The lesion is described as rough or flaky, raised or bumpy and fluid-filled. The affected area is the back of the hand, leg and arm. The photograph was taken at an angle. Self-categorized by the patient as a rash.
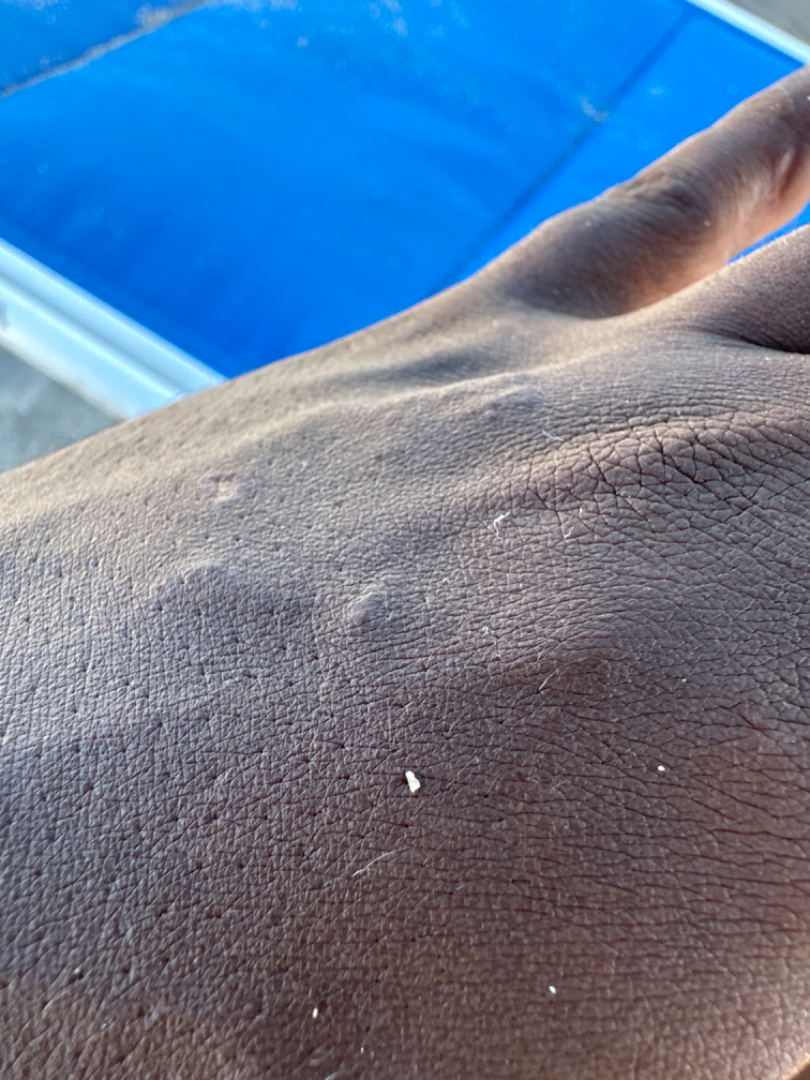{"assessment": "indeterminate from the photograph"}